A dermoscopic close-up of a skin lesion.
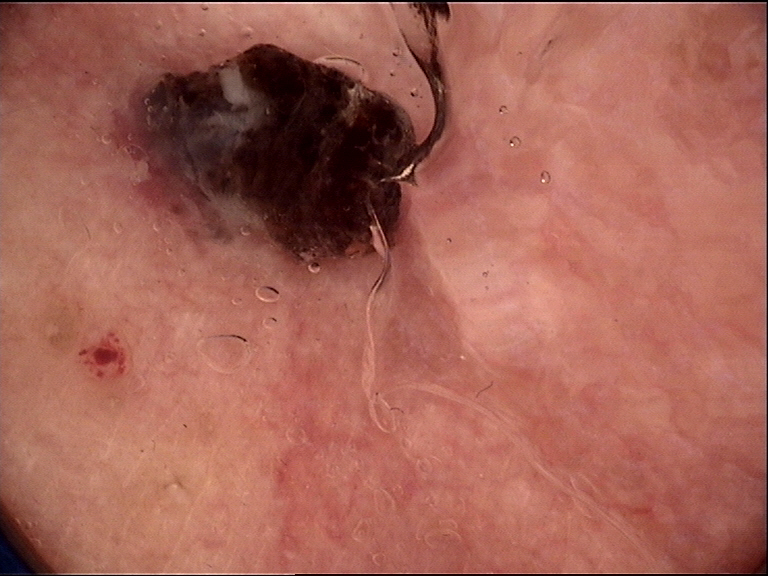label — melanoma (biopsy-proven).